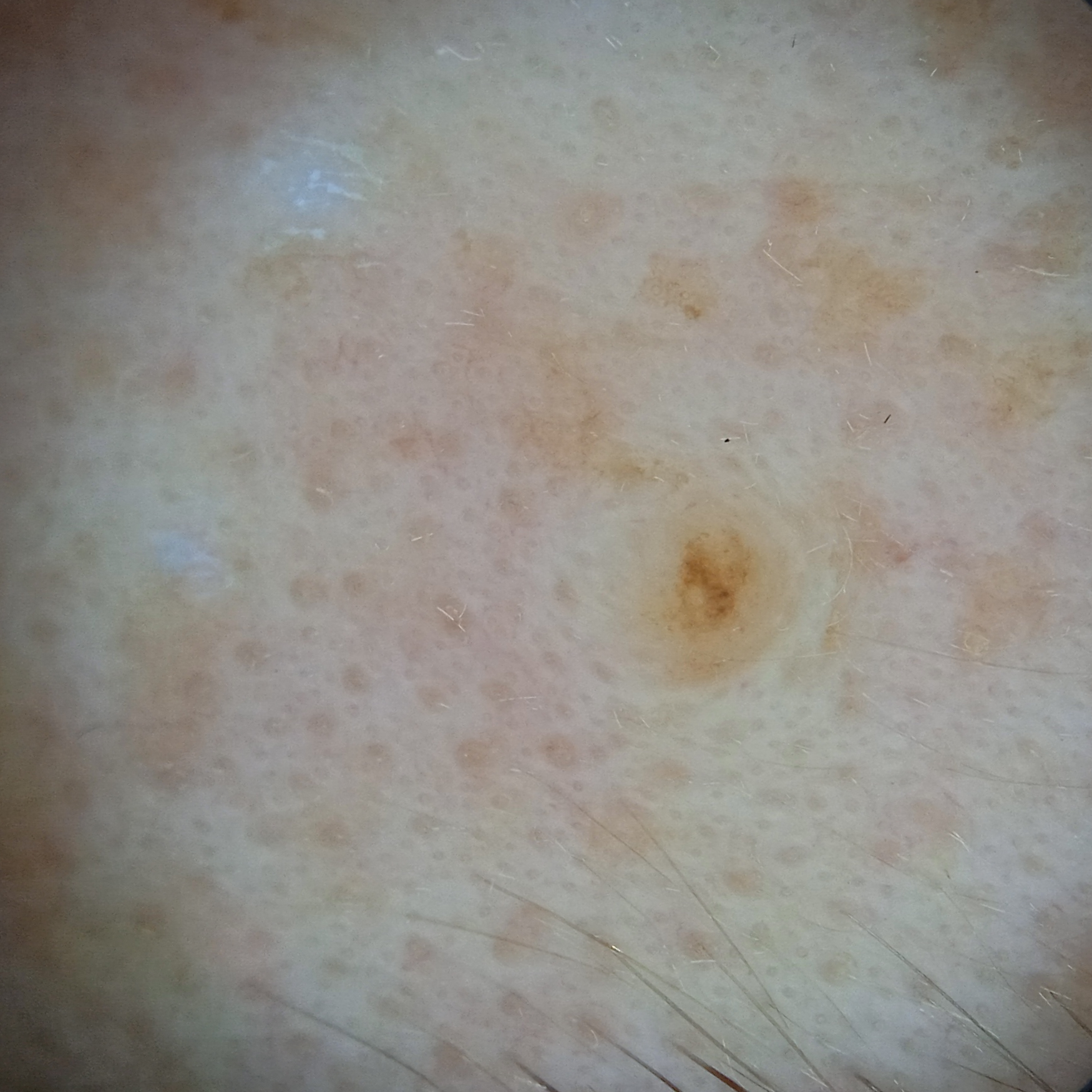Q: Patient demographics?
A: female, 50 years of age
Q: What kind of image is this?
A: dermoscopic image
Q: How does the patient's skin react to sun?
A: skin reddens painfully with sun exposure
Q: Where is the lesion?
A: the face
Q: Lesion size?
A: 1.8 mm
Q: What was the diagnosis?
A: melanocytic nevus (dermatologist consensus)